Acquired for a research image collection, with no referral diagnosis; a female patient 26 years of age — 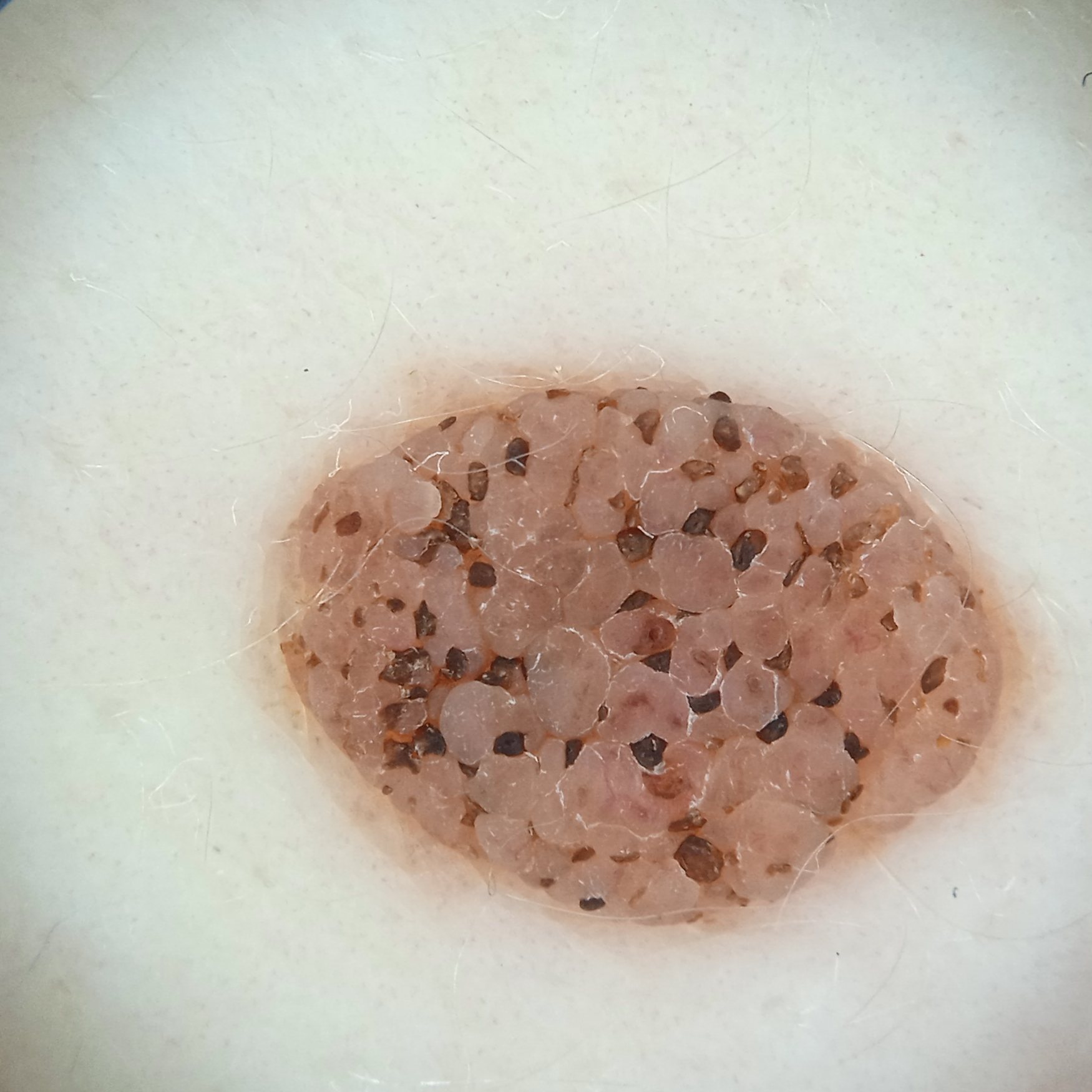Findings:
The lesion is about 8.4 mm across.
Assessment:
Dermatologist review favored a seborrheic keratosis.